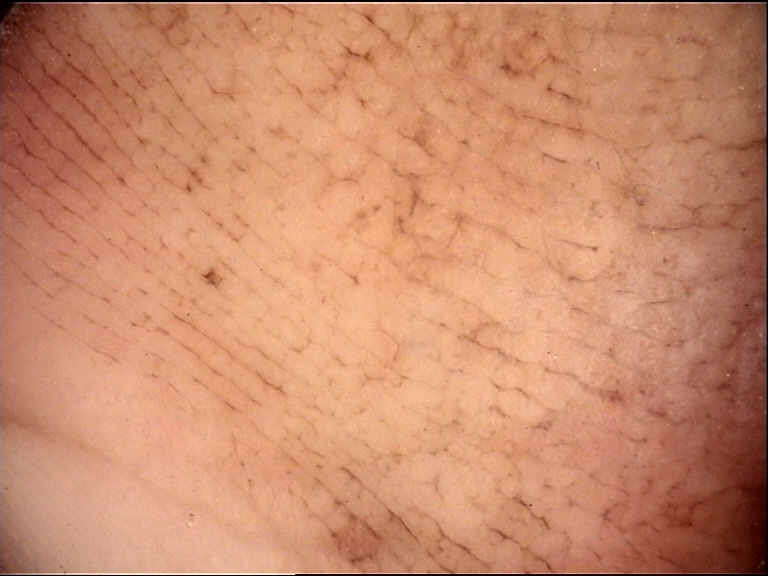A dermoscopy image of a single skin lesion.
This is a banal lesion.
Consistent with an acral junctional nevus.